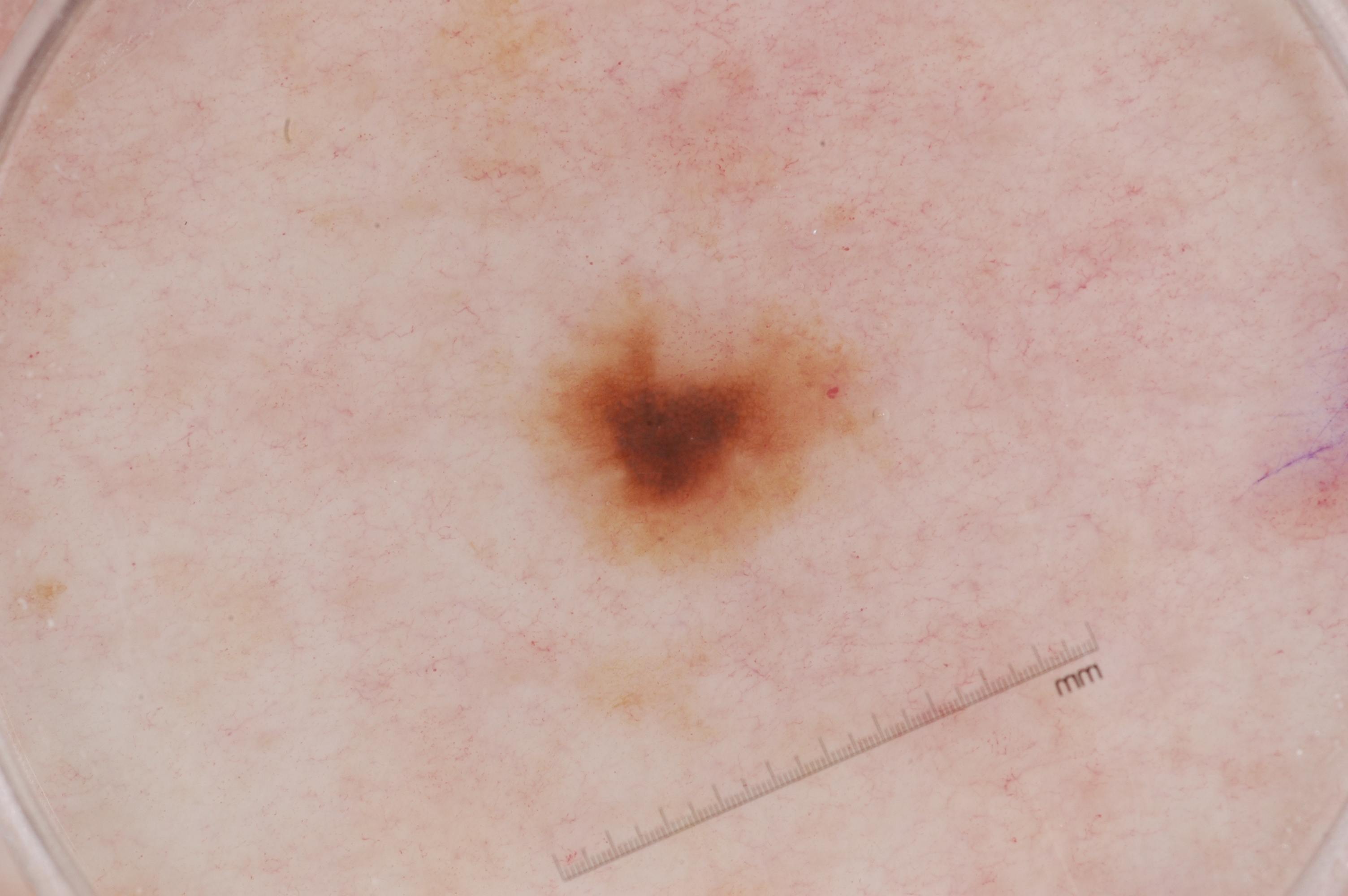Dermoscopy of a skin lesion. A male patient in their mid-60s. Dermoscopic review identifies pigment network, with no milia-like cysts, streaks, or negative network. As (left, top, right, bottom), lesion location: (537, 294, 874, 567). Diagnosed as a melanocytic nevus, a benign skin lesion.